An overview clinical photograph of a skin lesion · a female patient roughly 85 years of age or older.
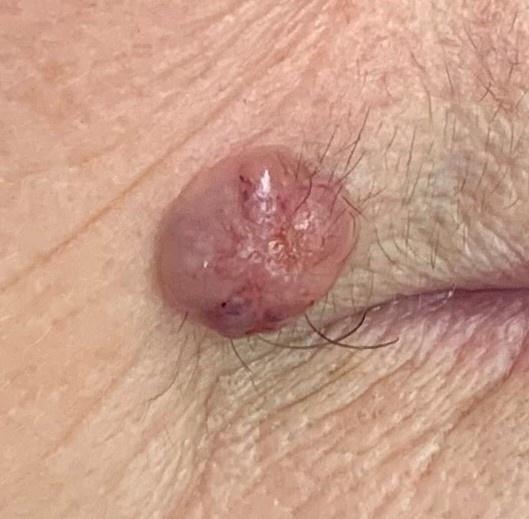<case>
<lesion_location>
<region>the head or neck</region>
</lesion_location>
<diagnosis>
<name>Basal cell carcinoma</name>
<malignancy>malignant</malignancy>
<confirmation>histopathology</confirmation>
<lineage>adnexal</lineage>
</diagnosis>
</case>